Dermoscopy of a skin lesion:
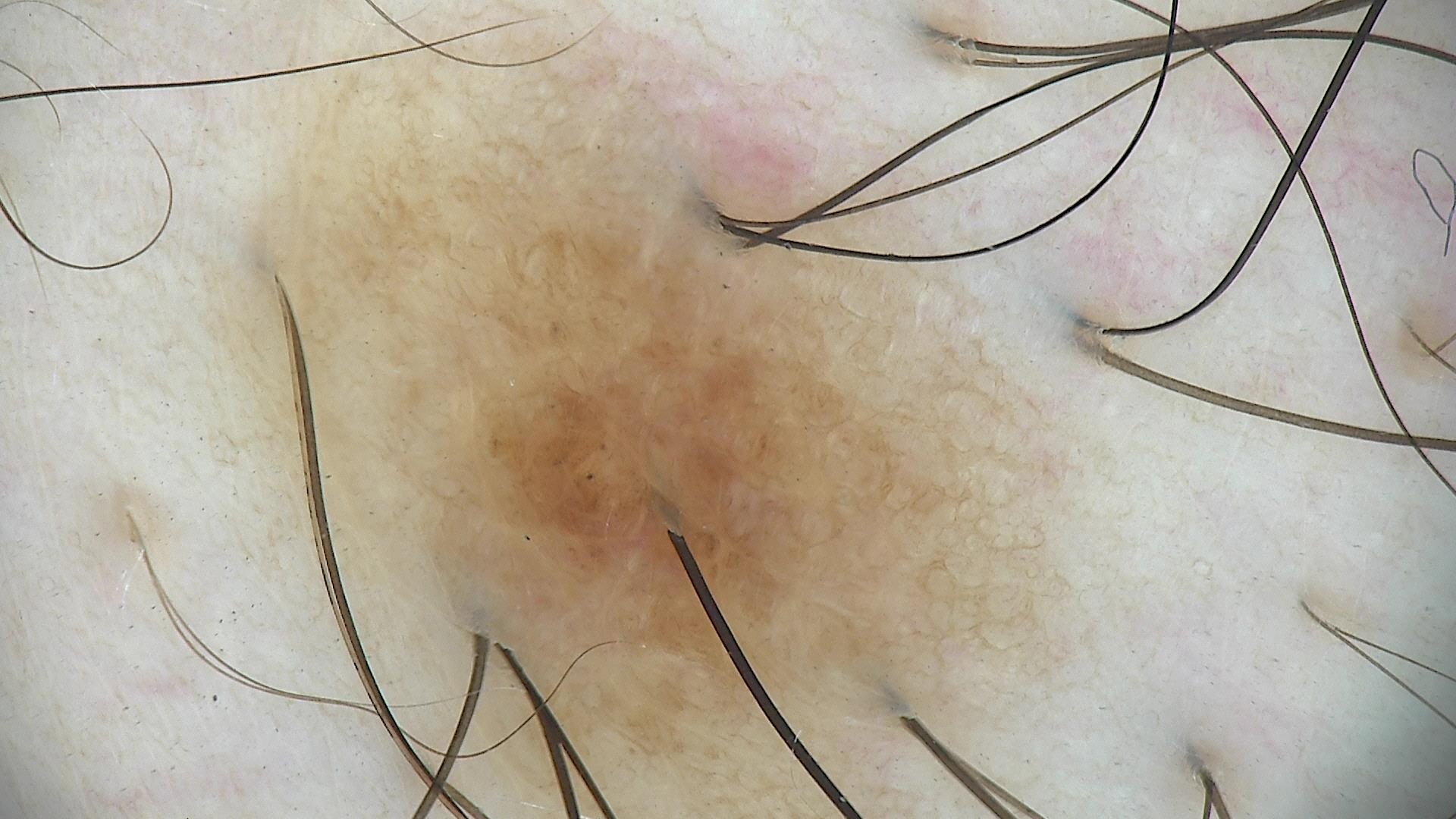The architecture is that of a banal lesion. The diagnosis was a compound nevus.